A dermoscopic image of a skin lesion: 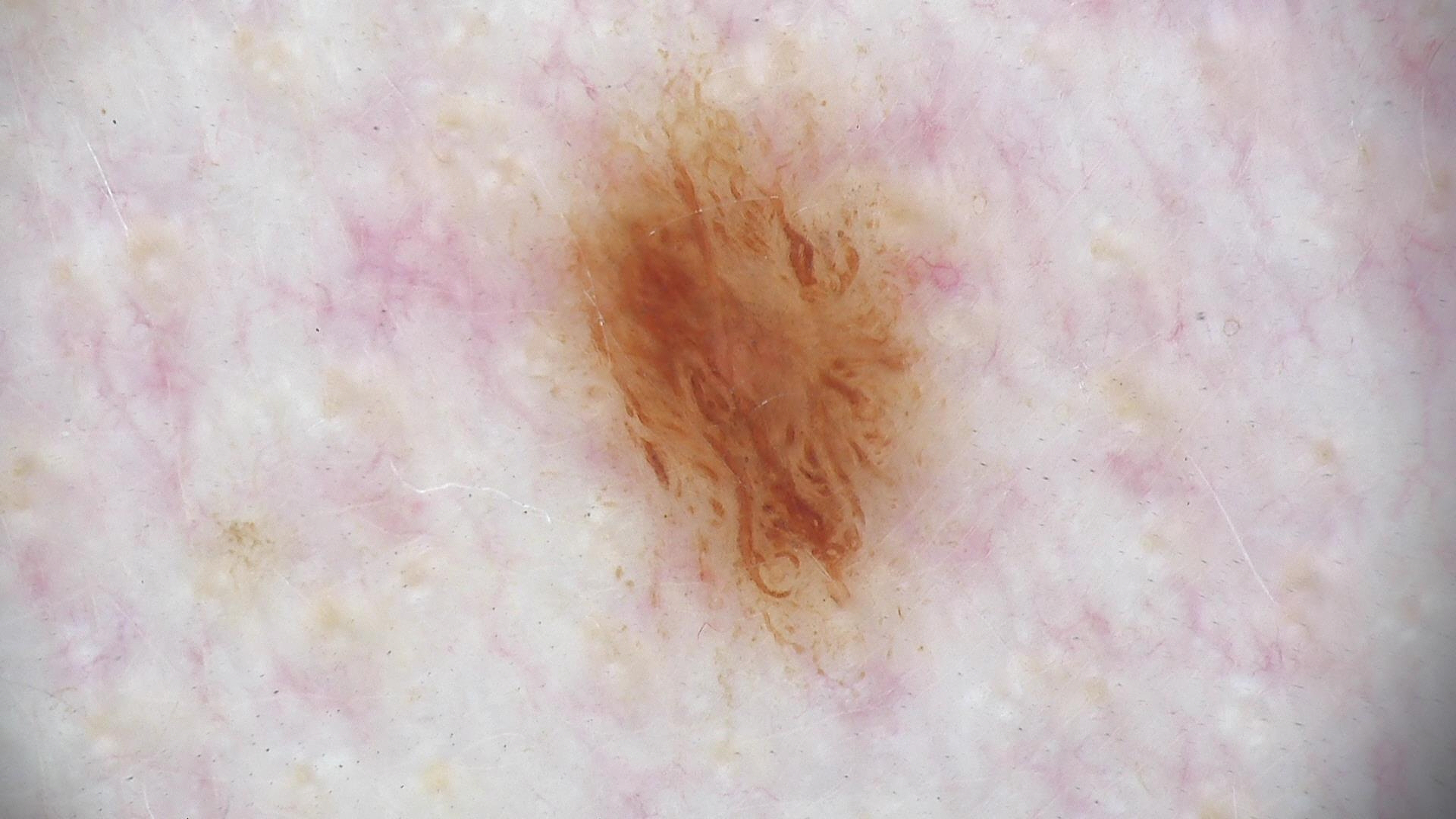assessment = dysplastic junctional nevus (expert consensus).